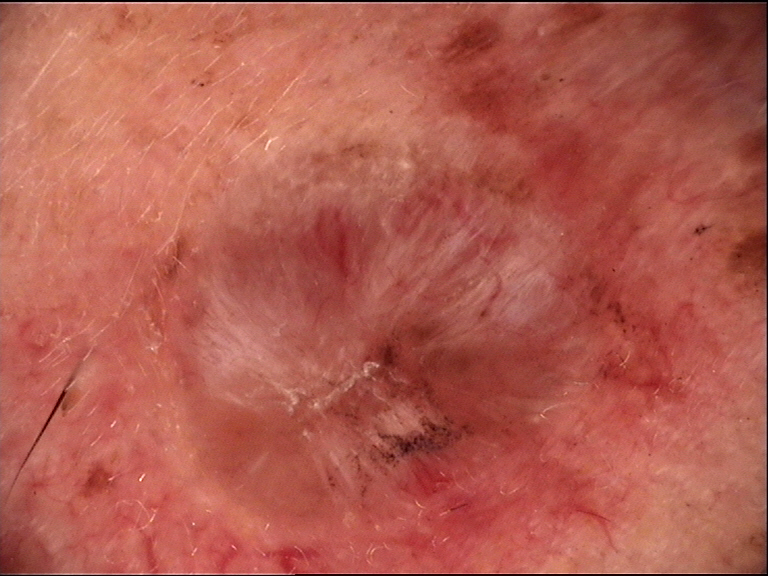Confirmed on histopathology as a keratinocytic, malignant lesion — a basal cell carcinoma.